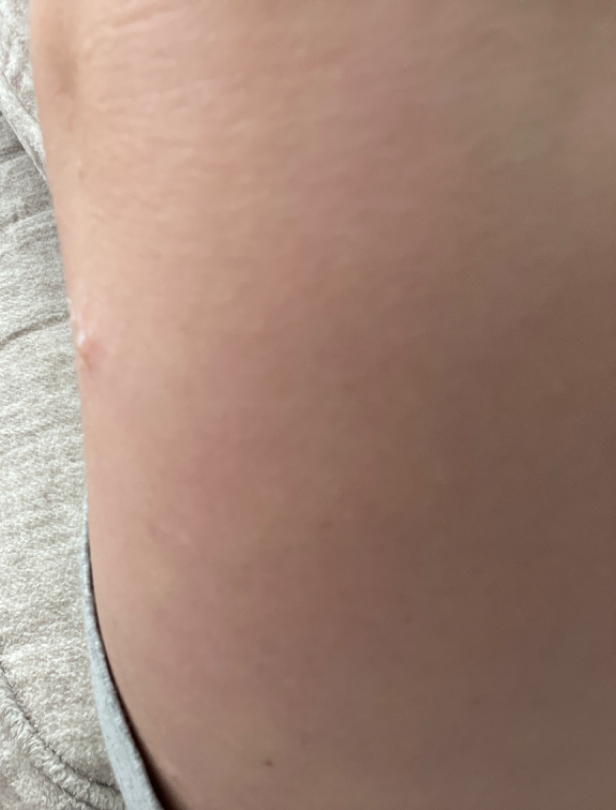assessment: unable to determine.